A male patient aged 33 to 37. Recorded as FST II. The chart records no previous melanoma and no melanoma in first-degree relatives. A skin lesion imaged with a dermatoscope.
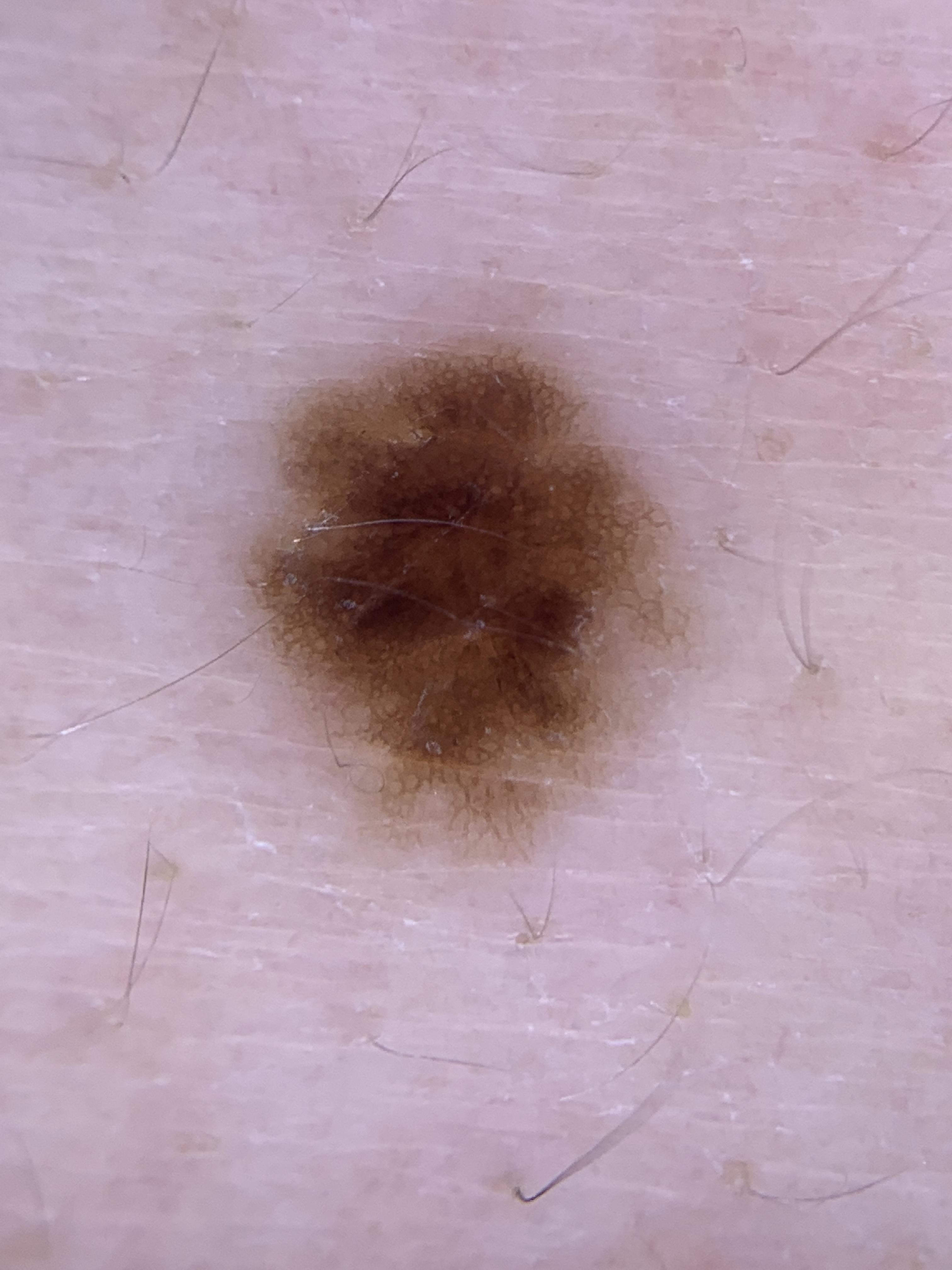Case:
* body site · the trunk
* diagnostic label · Nevus (biopsy-proven)